A dermoscopic image of a skin lesion.
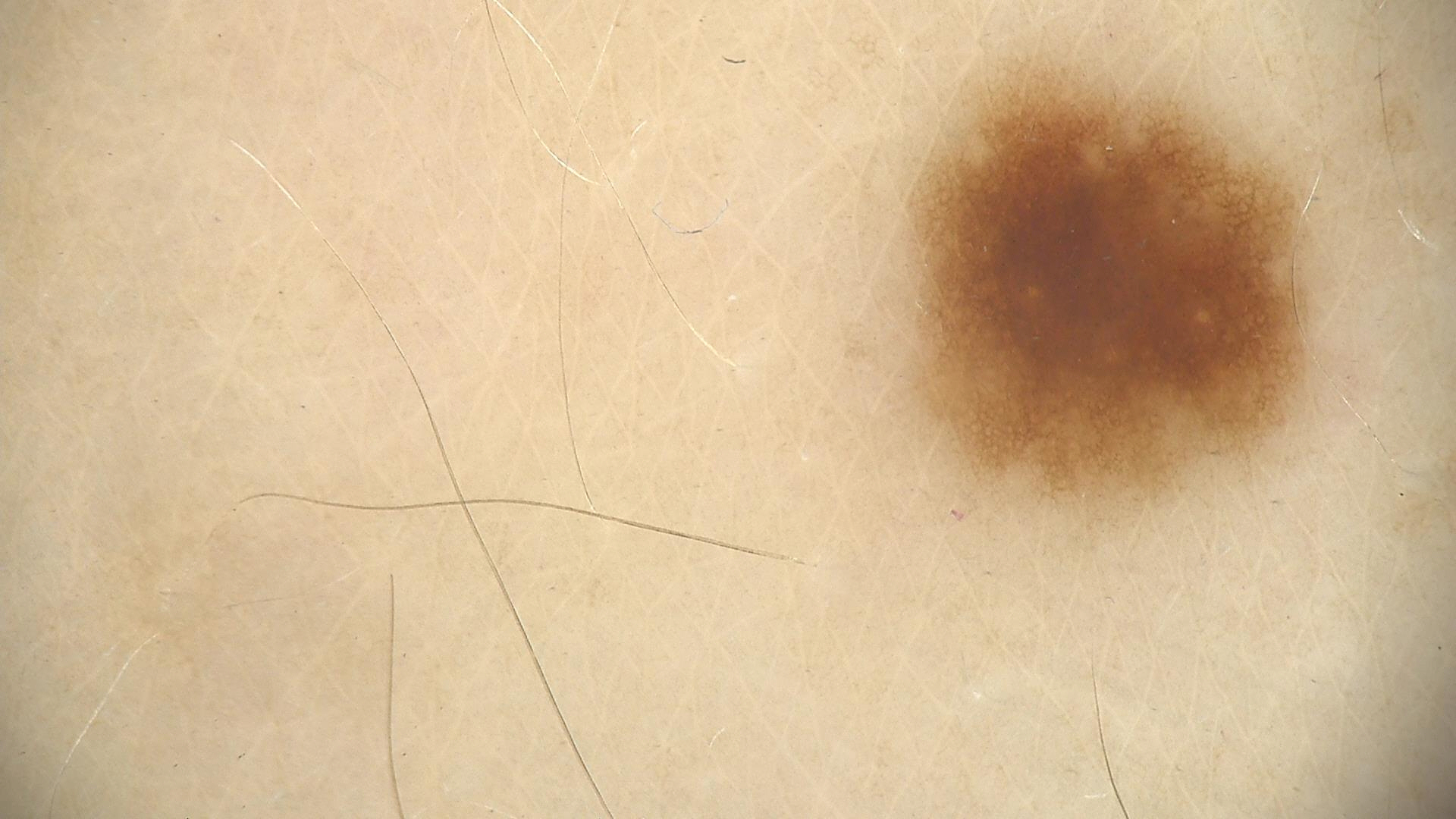Labeled as a dysplastic junctional nevus.